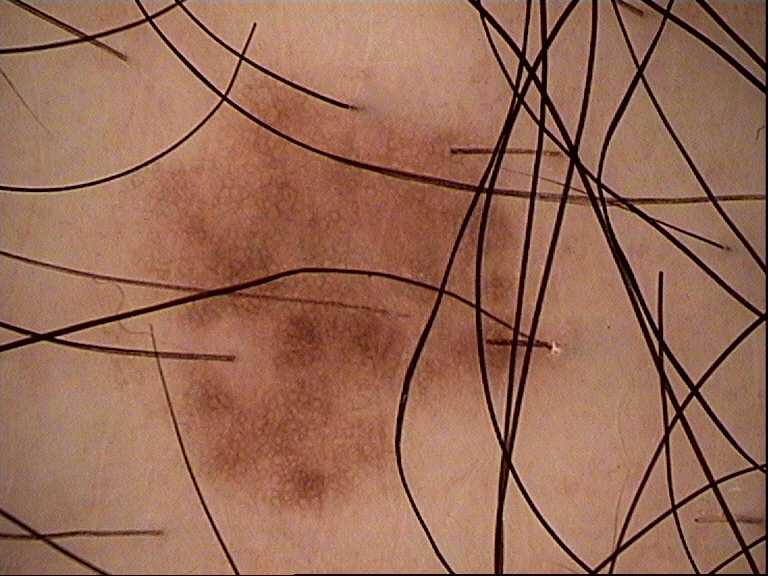A dermoscopic close-up of a skin lesion. Labeled as a benign lesion — a dysplastic junctional nevus.